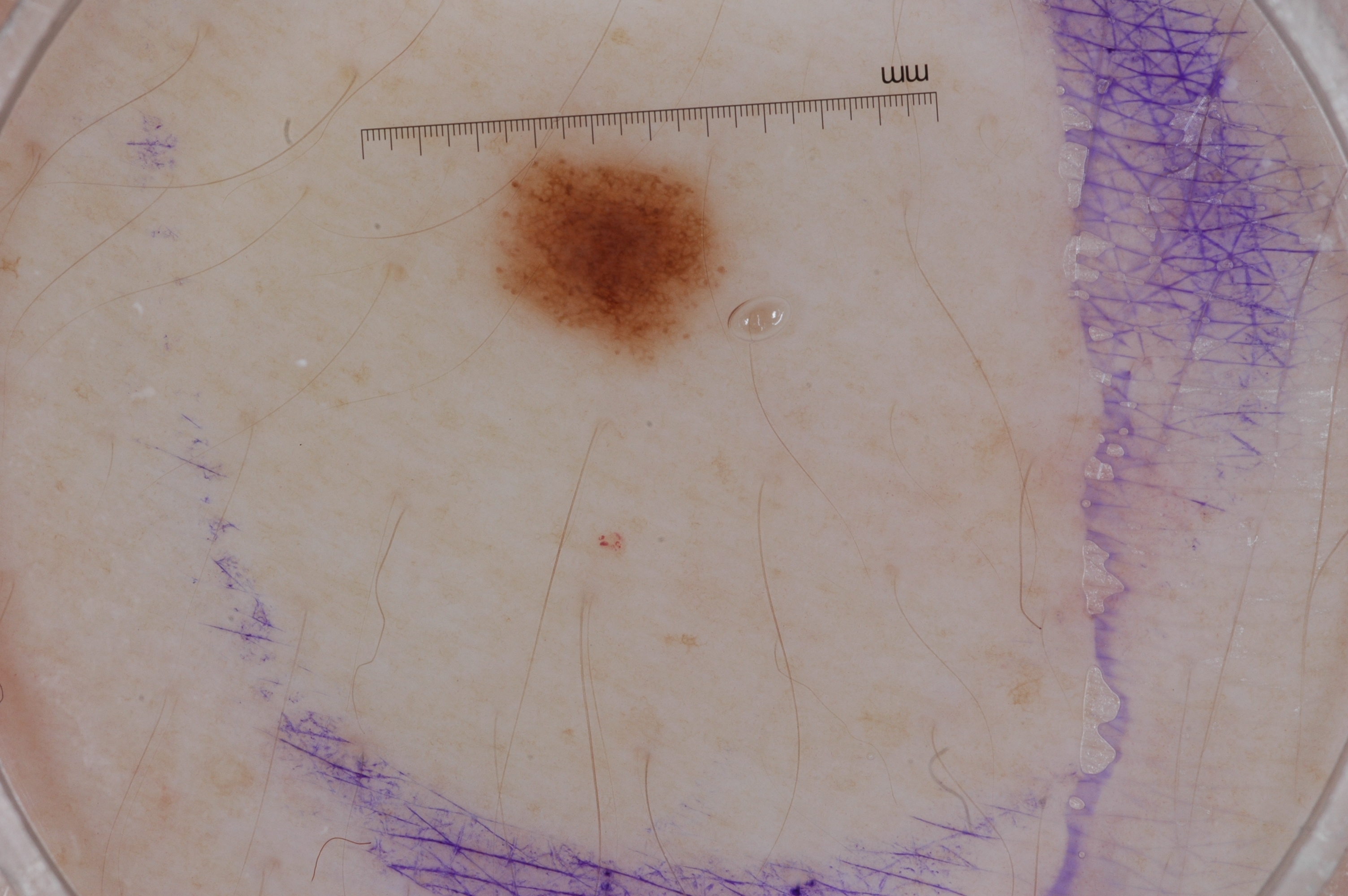subject: female, aged 23-27; modality: dermoscopy of a skin lesion; bounding box: <bbox>494, 145, 726, 361</bbox>; dermoscopic findings: pigment network; assessment: a melanocytic nevus.